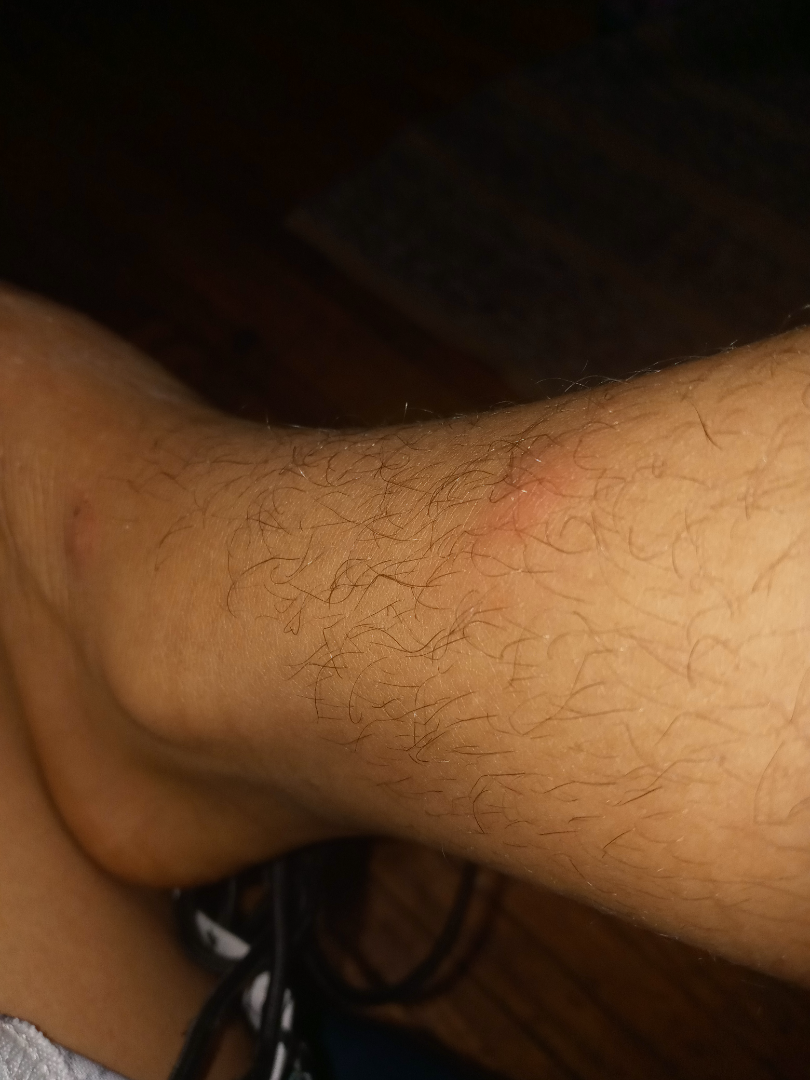Impression:
The skin findings could not be characterized from the image.
History:
Close-up view.